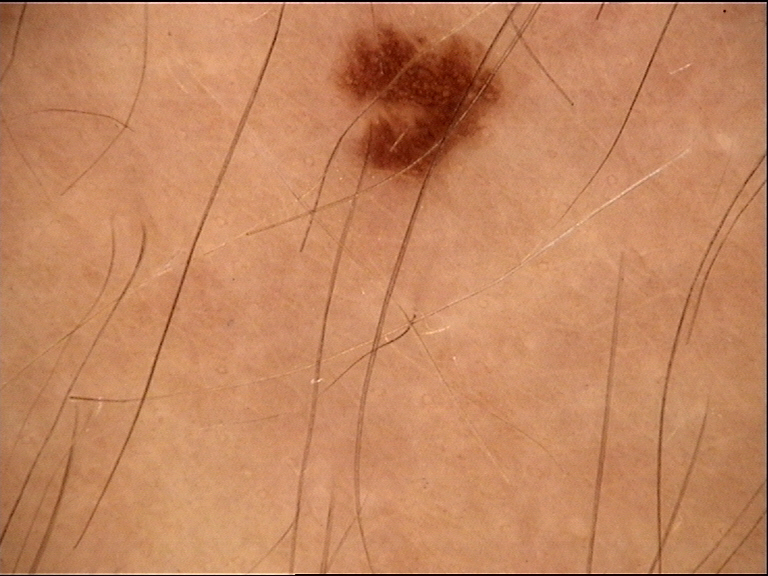{
  "image": "dermoscopy",
  "diagnosis": {
    "name": "dysplastic junctional nevus",
    "code": "jd",
    "malignancy": "benign",
    "super_class": "melanocytic",
    "confirmation": "expert consensus"
  }
}